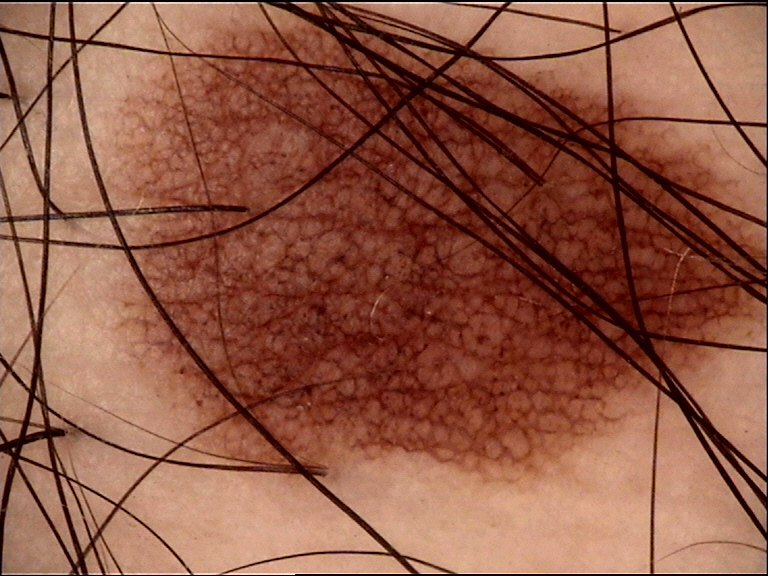modality — dermatoscopy
label — dysplastic junctional nevus (expert consensus)